The subject is a female aged 70–79 · the leg is involved · the photograph is a close-up of the affected area — 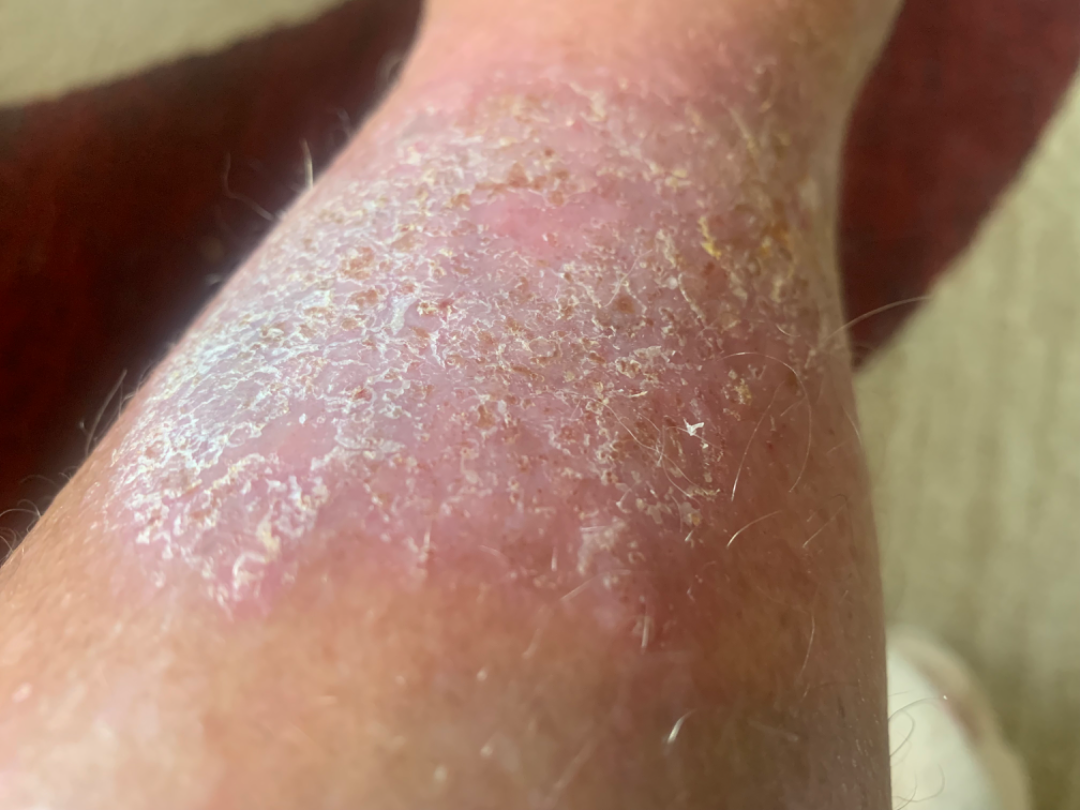Most consistent with Infected eczema; with consideration of Psoriasis; an alternative is Lichen Simplex Chronicus.